Texture is reported as fluid-filled and raised or bumpy. The photograph is a close-up of the affected area. No associated systemic symptoms reported. The palm and back of the hand are involved. The patient is a female aged 40–49 — 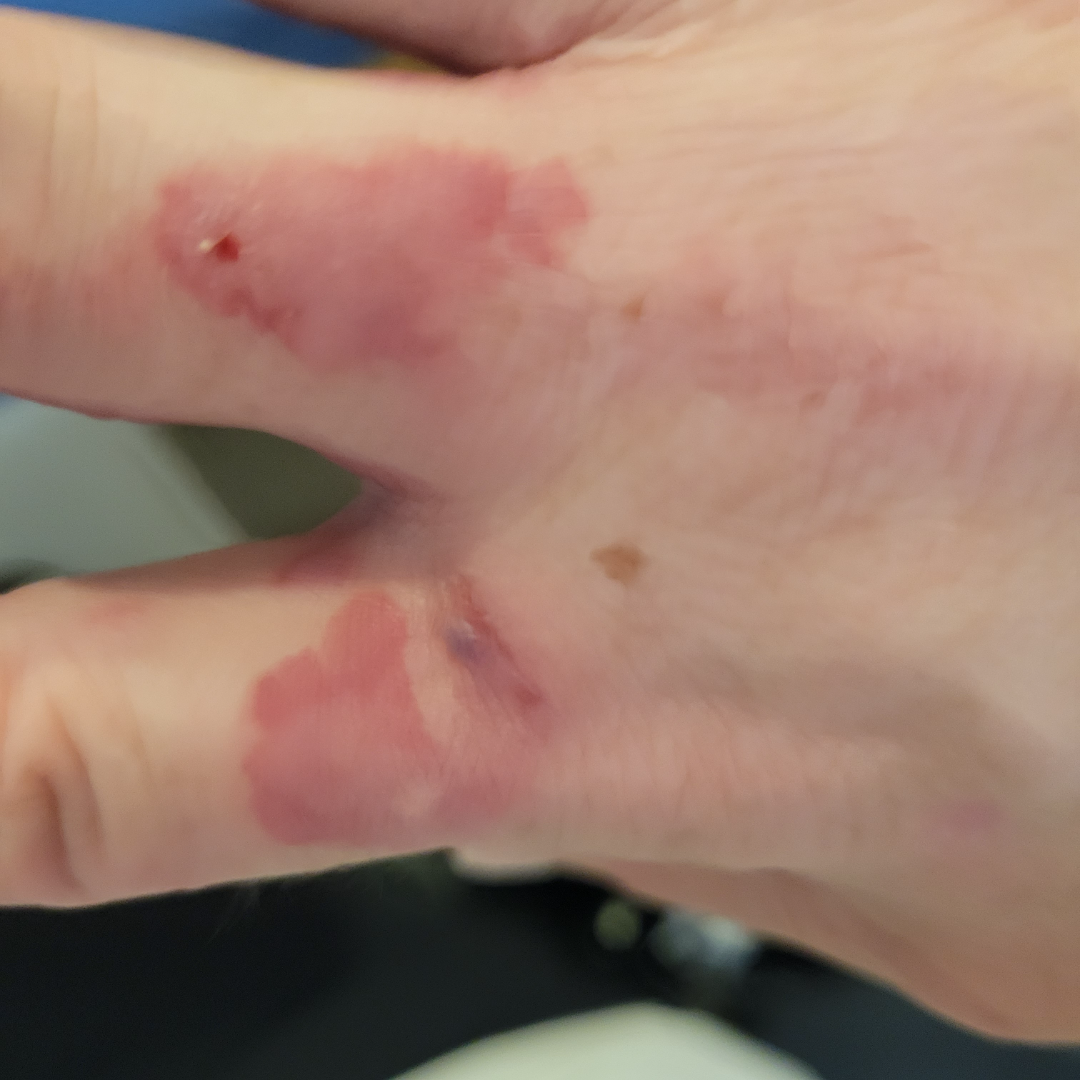{
  "differential": {
    "Tinea": 0.33,
    "Burn of skin": 0.33,
    "Allergic Contact Dermatitis": 0.33
  }
}